The patient reports itching; associated systemic symptoms include fatigue; located on the front of the torso; the condition has been present for about one day; the patient reports the lesion is raised or bumpy; the patient is 30–39, female; self-categorized by the patient as a rash; Fitzpatrick III; the photo was captured at a distance:
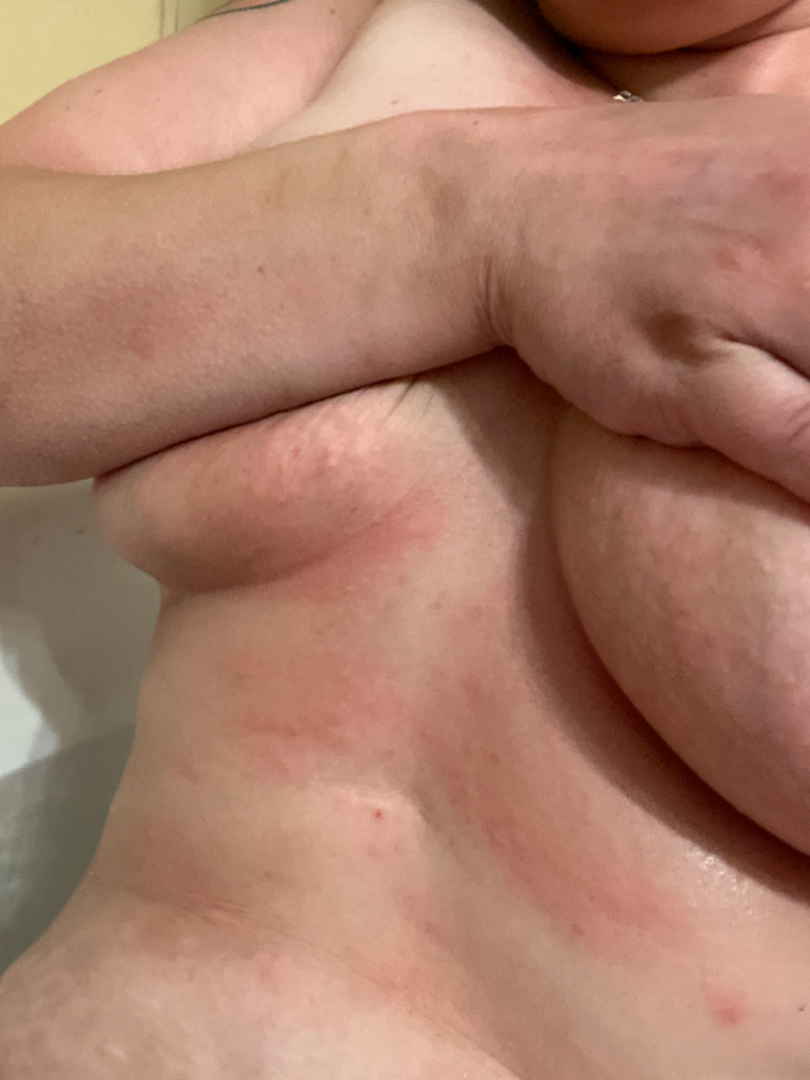Diagnostic features were not clearly distinguishable in this photograph.